A dermoscopic photograph of a skin lesion.
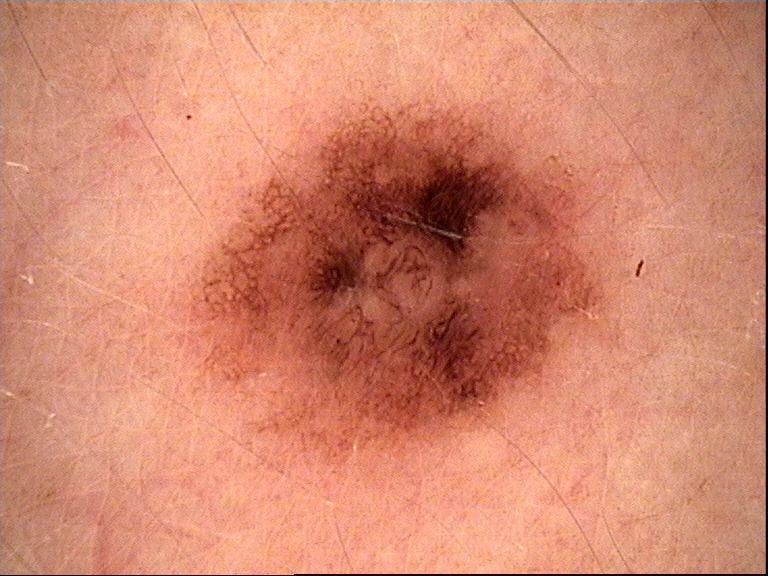| key | value |
|---|---|
| diagnosis | dysplastic compound nevus (expert consensus) |